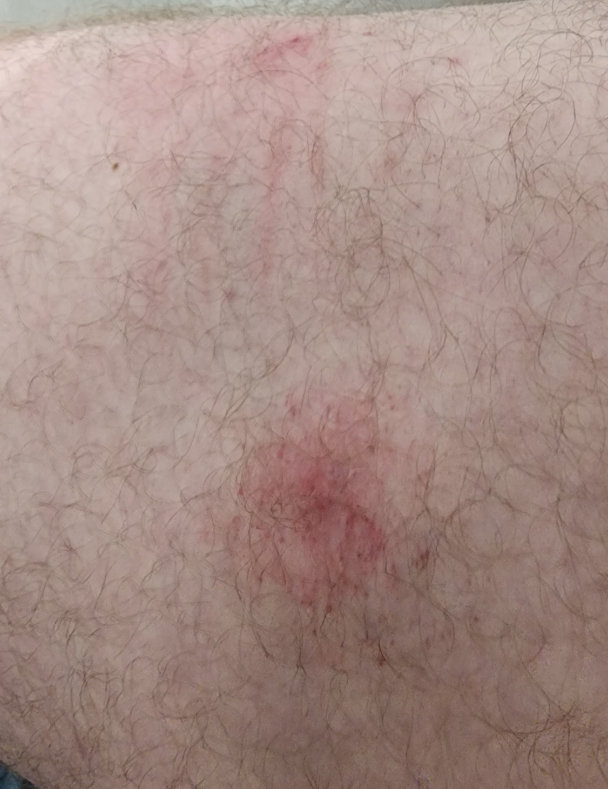assessment: indeterminate
patient_category: a rash
symptoms:
  - enlargement
  - bleeding
  - itching
body_site: leg
shot_type: at an angle
texture:
  - raised or bumpy
  - fluid-filled
systemic_symptoms: none reported
duration: less than one week